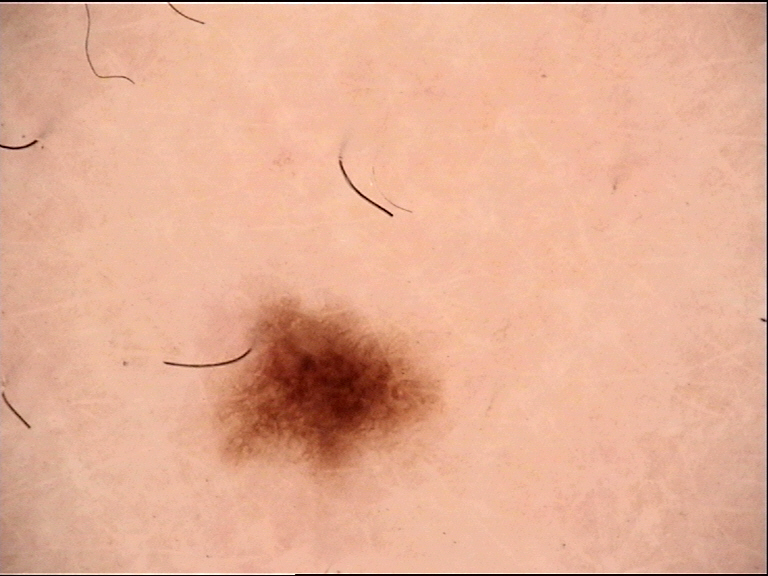* lesion type: banal
* label: junctional nevus (expert consensus)